A female subject approximately 60 years of age. A dermoscopic close-up of a skin lesion — 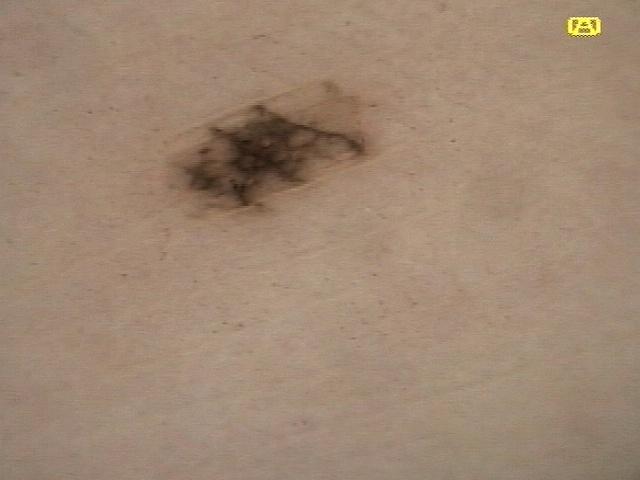Case:
– location · an upper extremity
– pathology · Nevus (biopsy-proven)